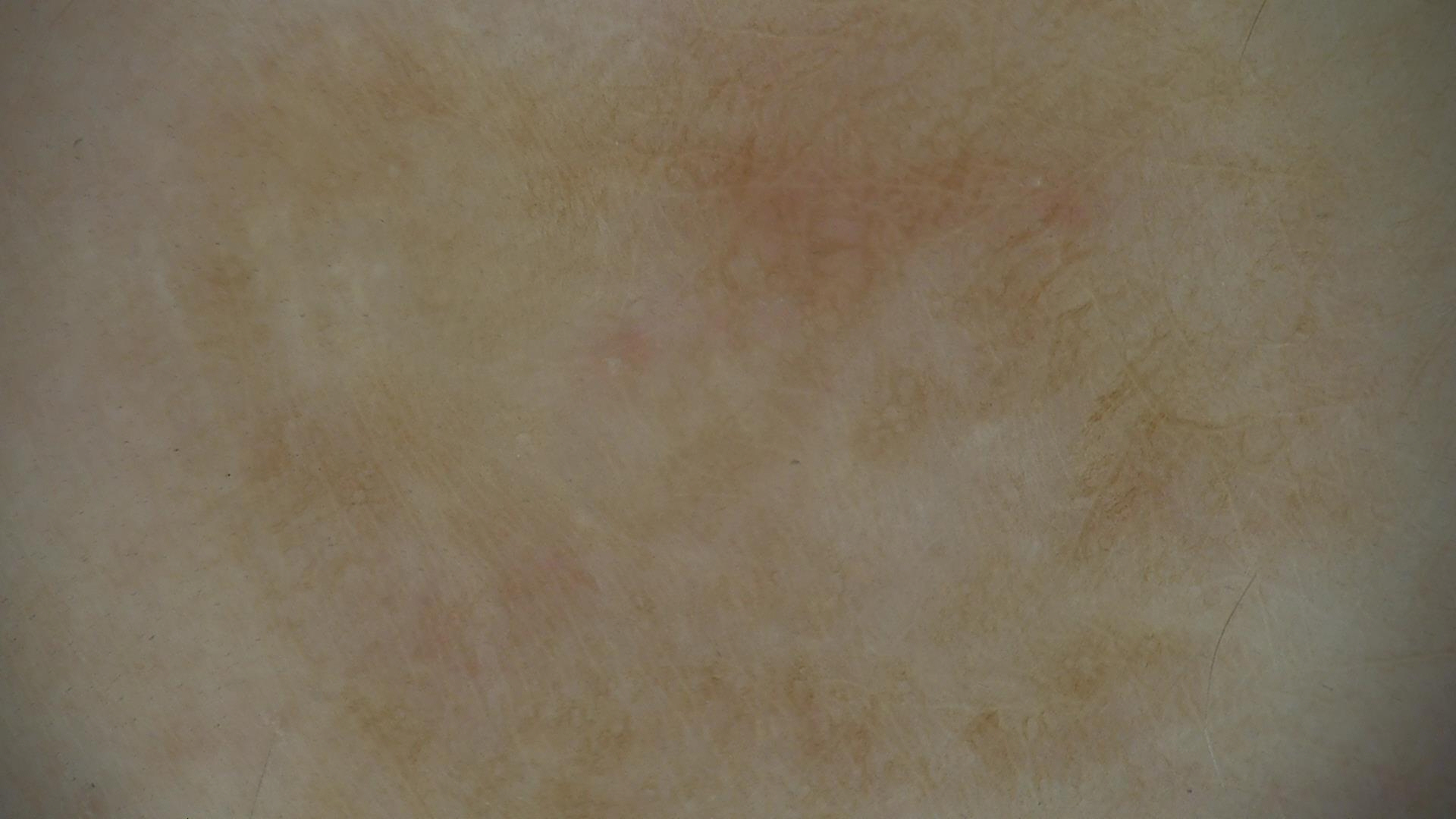Findings: A dermoscopic image of a skin lesion. Conclusion: Labeled as a benign lesion — a recurrent nevus.